Dermoscopy of a skin lesion.
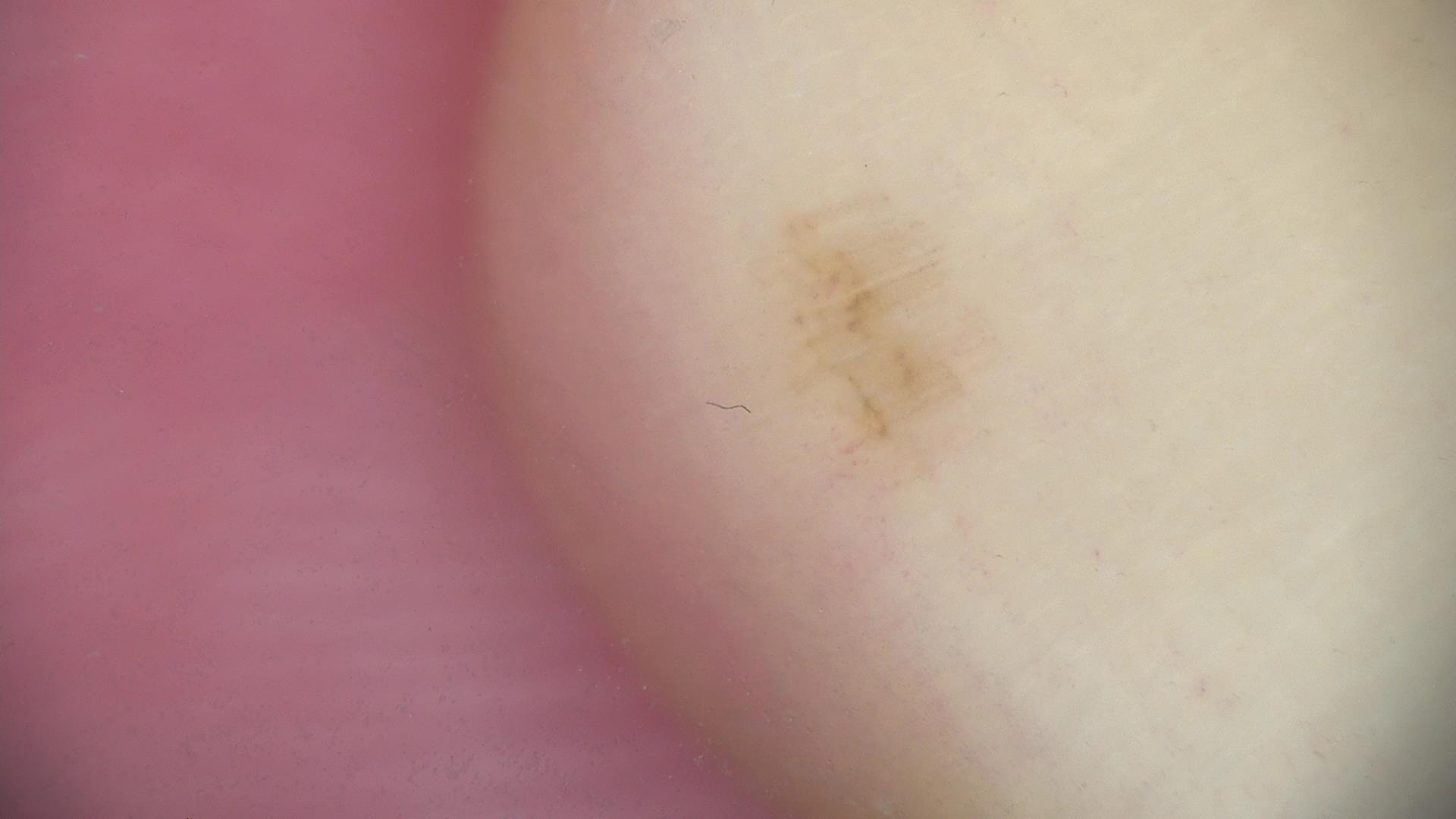| field | value |
|---|---|
| class | acral dysplastic junctional nevus (expert consensus) |